A clinical photo of a skin lesion taken with a smartphone · a male patient in their 70s · by history, no alcohol use and no tobacco use:
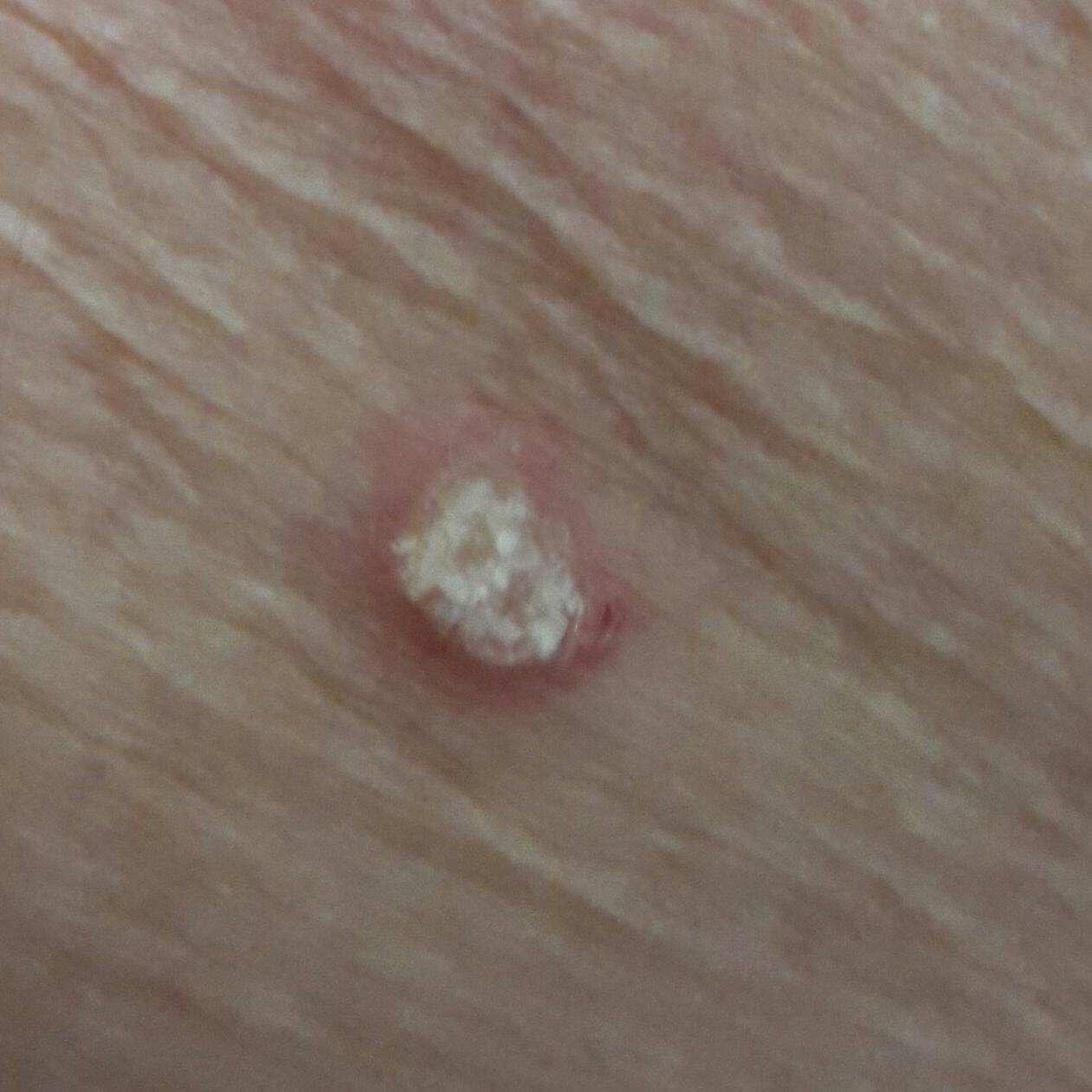Clinical context: The lesion involves an arm. The patient reports that the lesion has grown and is elevated. Conclusion: The biopsy diagnosis was an actinic keratosis.